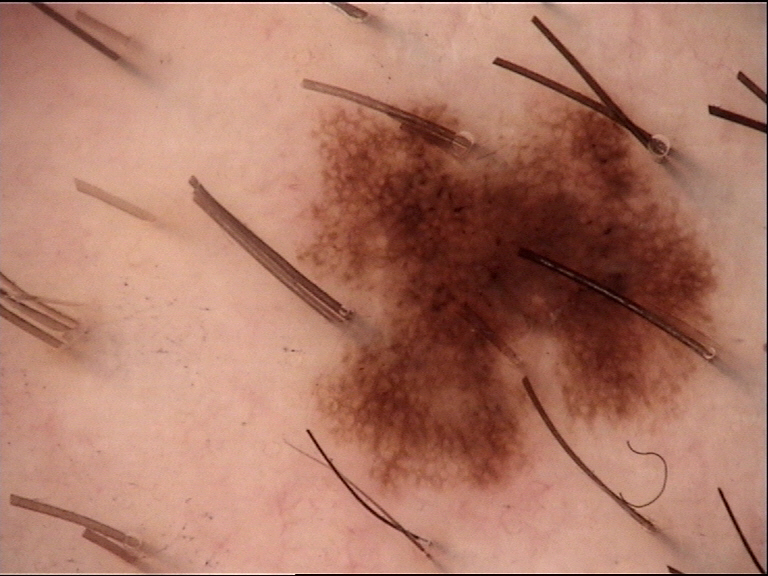label: dysplastic junctional nevus (expert consensus).